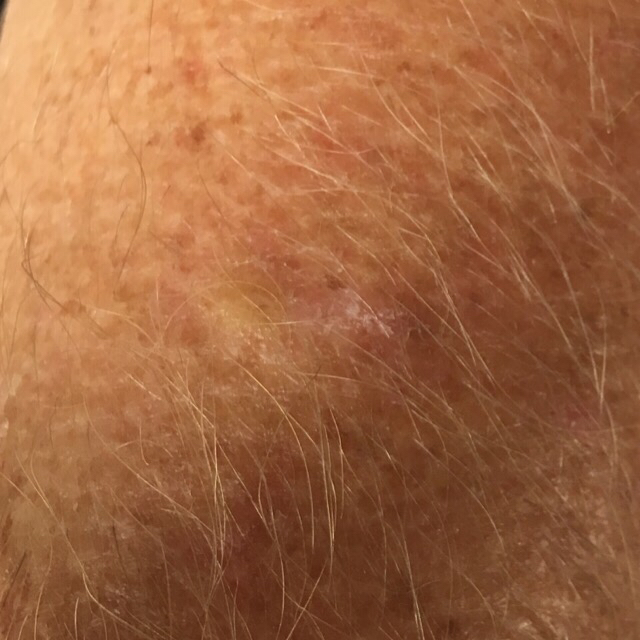Case summary:
A female patient aged 55. The lesion was found on an arm. Per patient report, the lesion itches.
Impression:
Clinically diagnosed as an actinic keratosis.